An image taken at an angle, located on the arm — 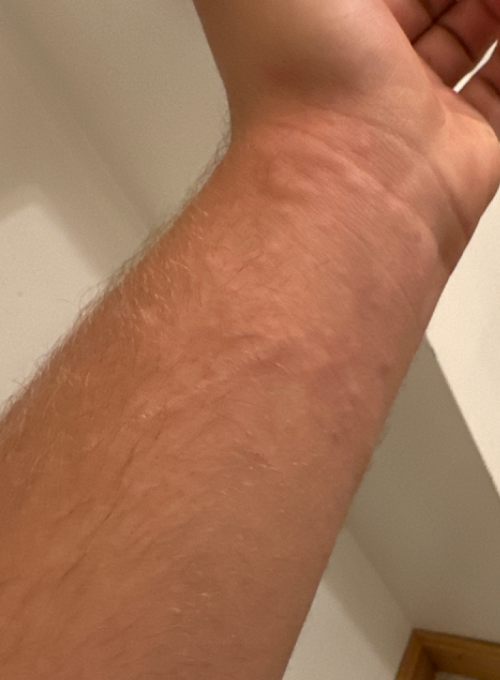Patient information: Reported duration is less than one week. The contributor notes the lesion is raised or bumpy. The patient considered this a rash. The lesion is associated with itching and burning. Fitzpatrick III; lay graders estimated MST 3 or 4. Review: Single-reviewer assessment: most likely Urticaria; also on the differential is Insect Bite; an alternative is Allergic Contact Dermatitis.